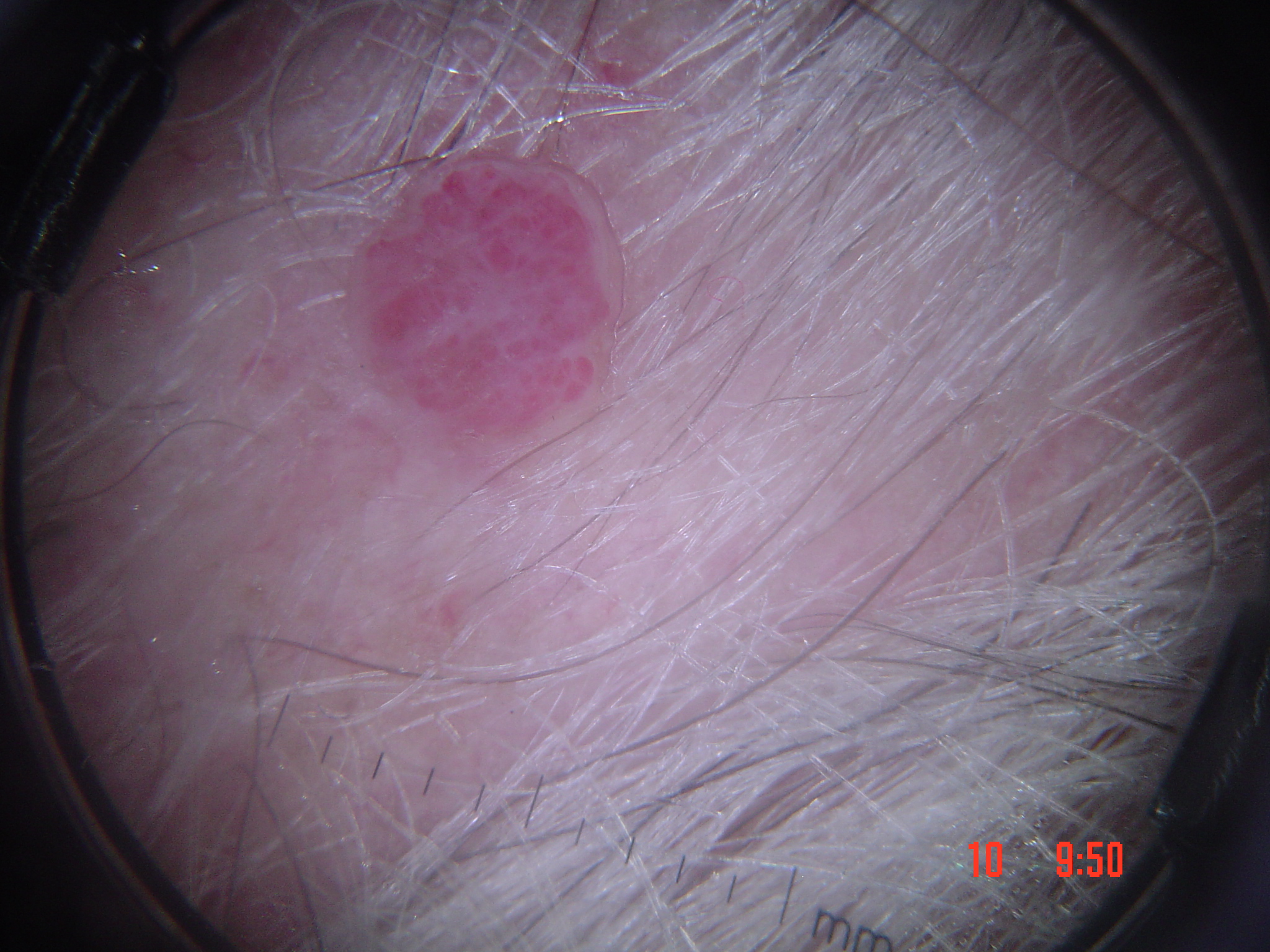Case: A dermoscopic image of a skin lesion. Impression: The diagnostic label was a benign, vascular lesion — a hemangioma.